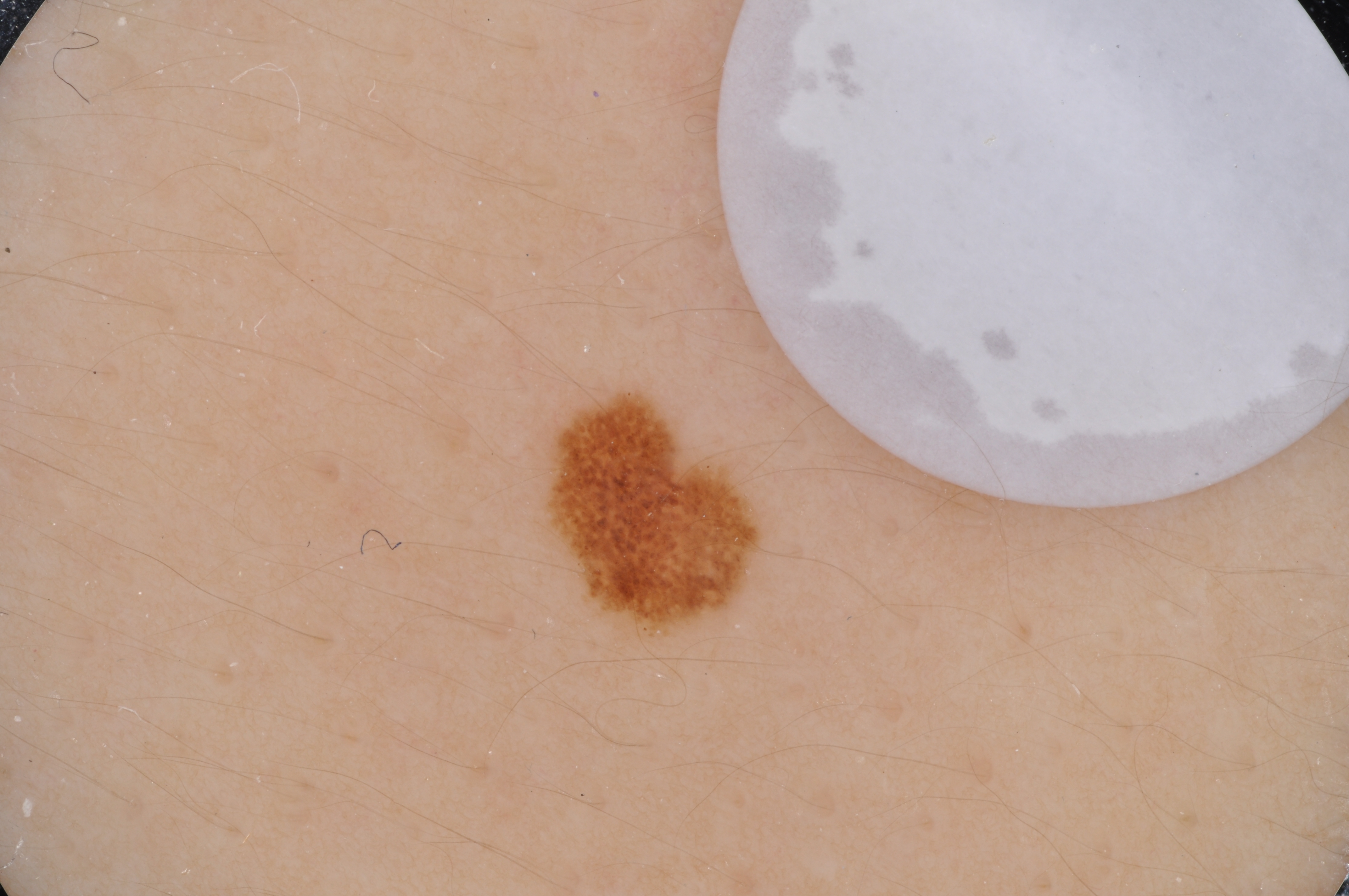- imaging · dermoscopy of a skin lesion
- subject · female, about 15 years old
- lesion bbox · bbox=[545, 393, 762, 642]
- lesion extent · small
- features · globules; absent: milia-like cysts, streaks, pigment network, and negative network
- assessment · a melanocytic nevus, a benign skin lesion